A skin lesion imaged with a dermatoscope, a female subject aged approximately 85 or older: 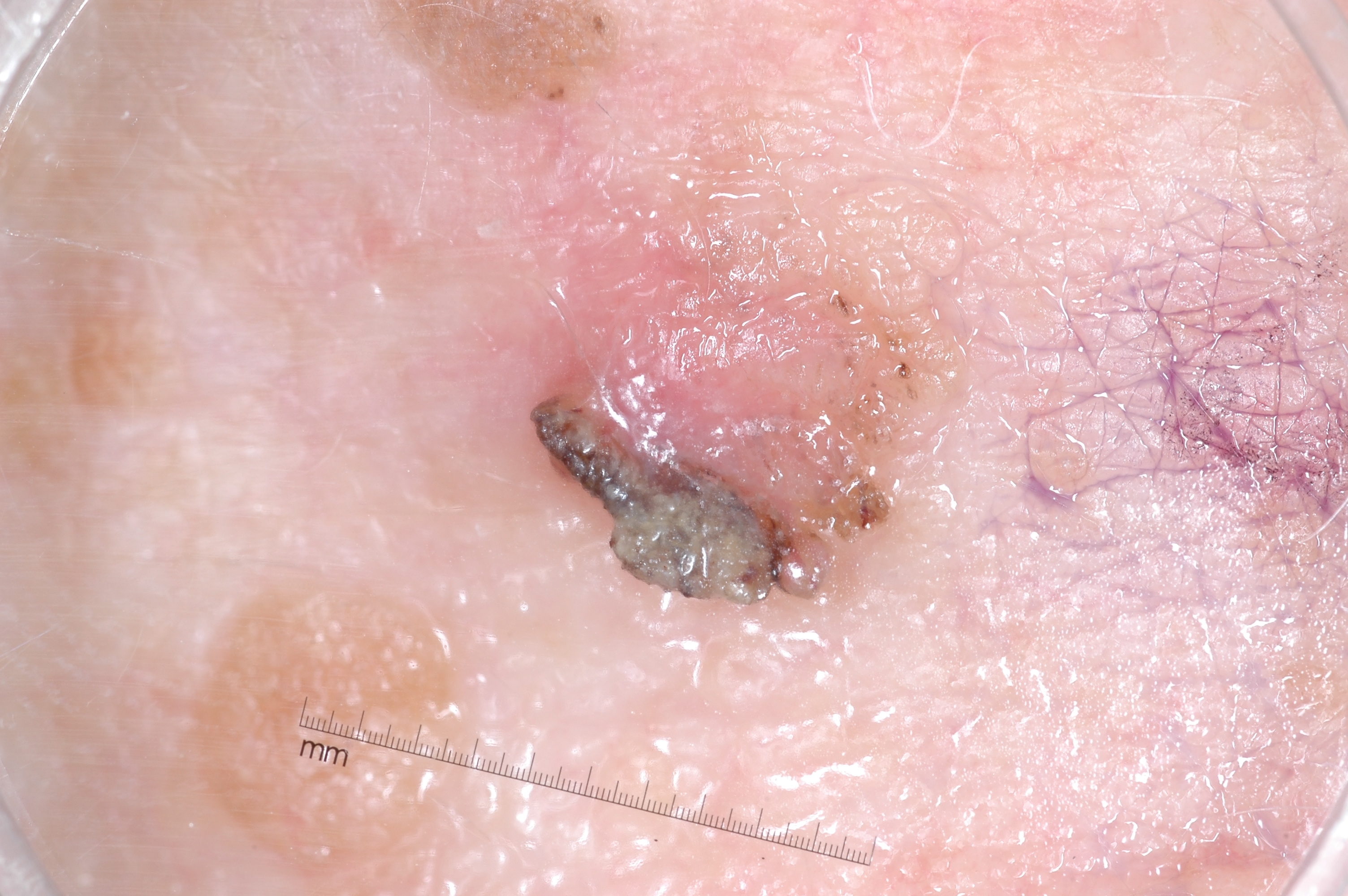absent dermoscopic features = pigment network, negative network, milia-like cysts, and streaks
location = 516, 105, 986, 622
lesion extent = moderate
diagnosis = a seborrheic keratosis